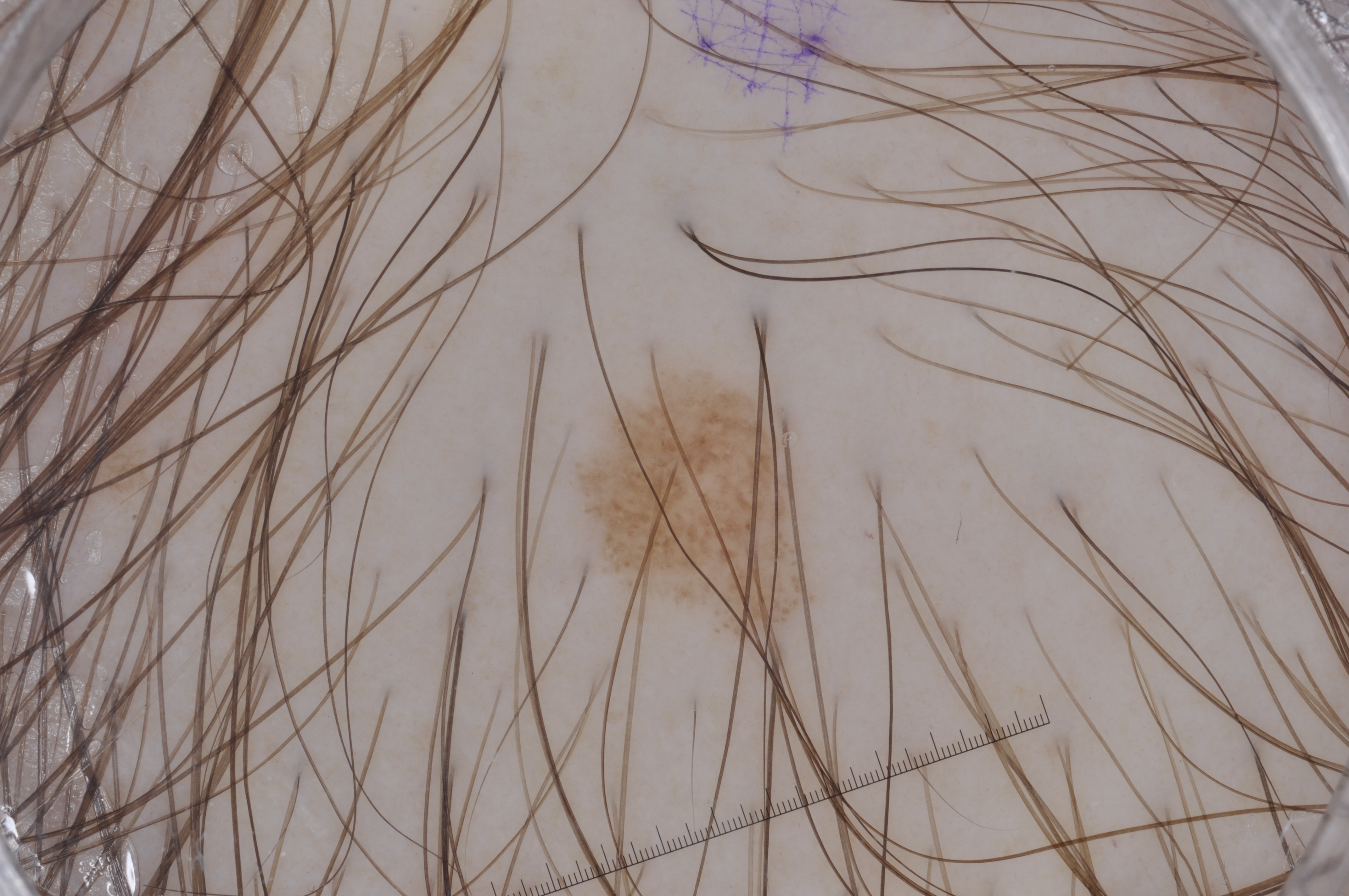patient: male, roughly 40 years of age; modality: dermoscopic image; absent dermoscopic features: negative network, streaks, milia-like cysts, and pigment network; size: ~5% of the field; lesion location: 566/346/825/653; diagnostic label: a melanocytic nevus, a benign skin lesion.